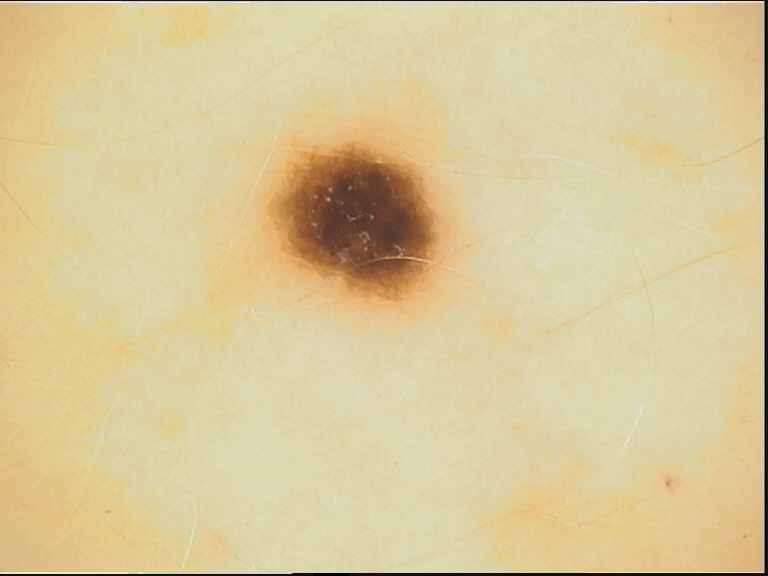diagnostic label = dysplastic junctional nevus (expert consensus).